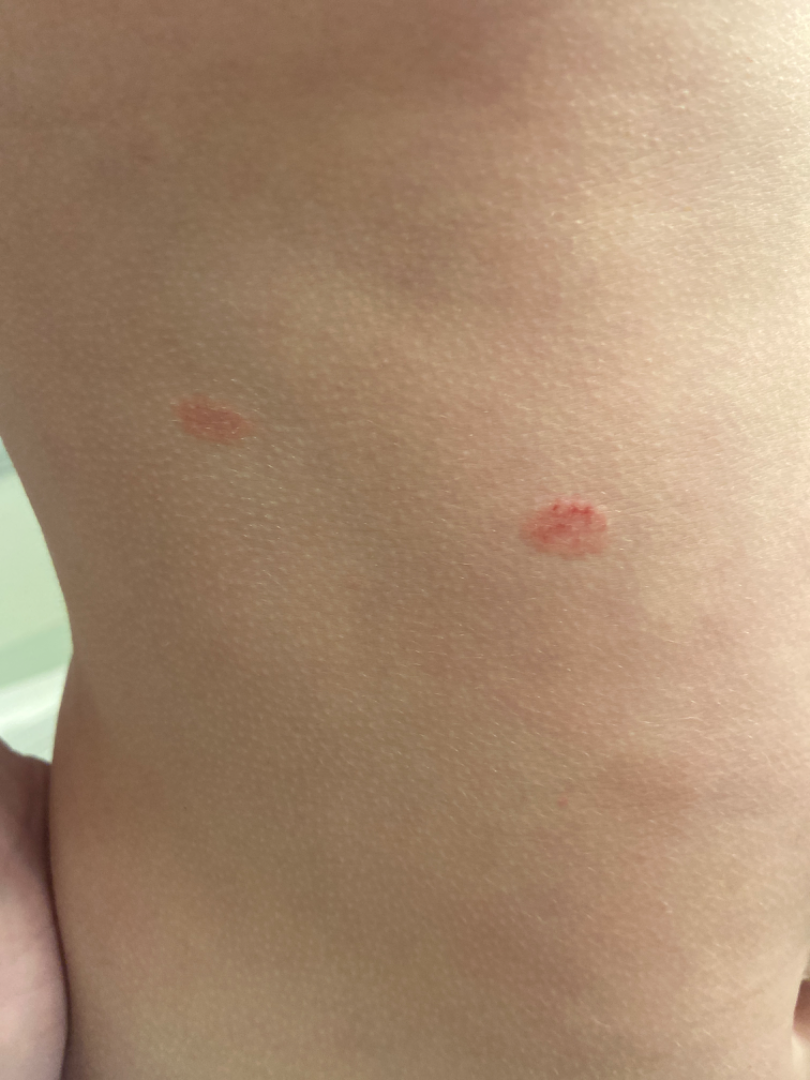The patient reports the lesion is raised or bumpy.
The subject is female.
Reported duration is one to four weeks.
This image was taken at a distance.
Located on the front of the torso and back of the torso.
Self-categorized by the patient as a rash.
On photographic review by a dermatologist, Pityriasis rosea (weight 0.55); Psoriasis (weight 0.27); Eczema (weight 0.18).